This image was taken at an angle: 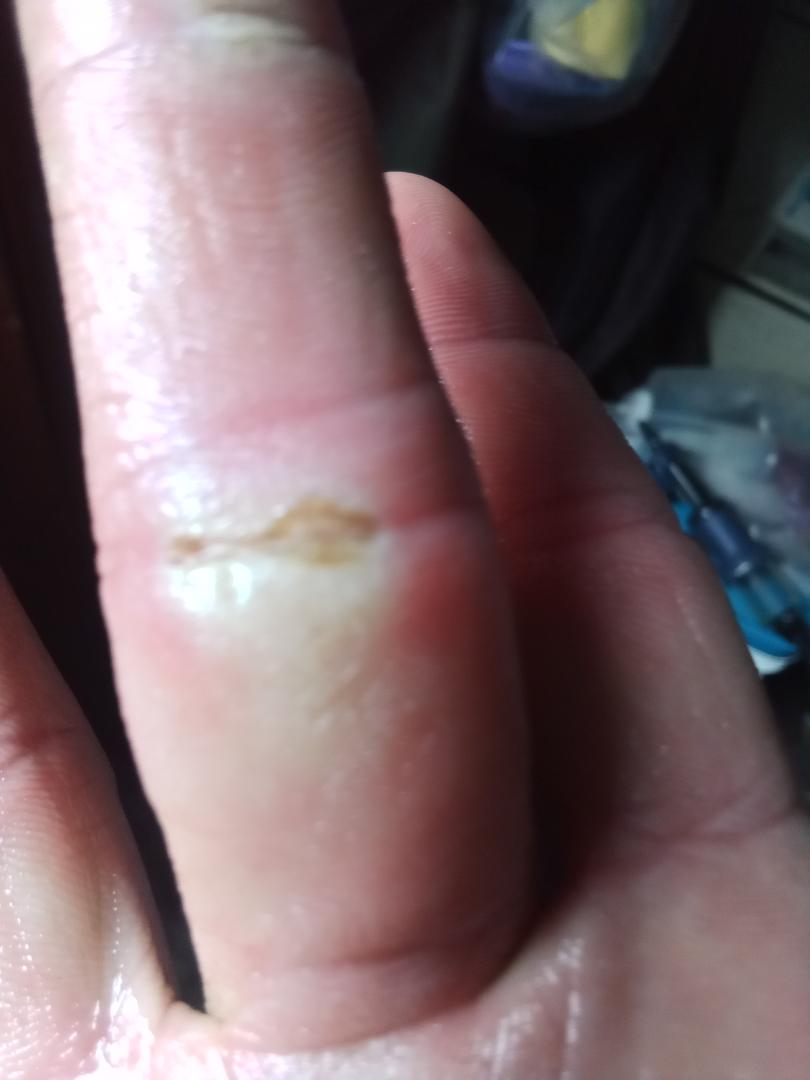Consistent with Irritant Contact Dermatitis.